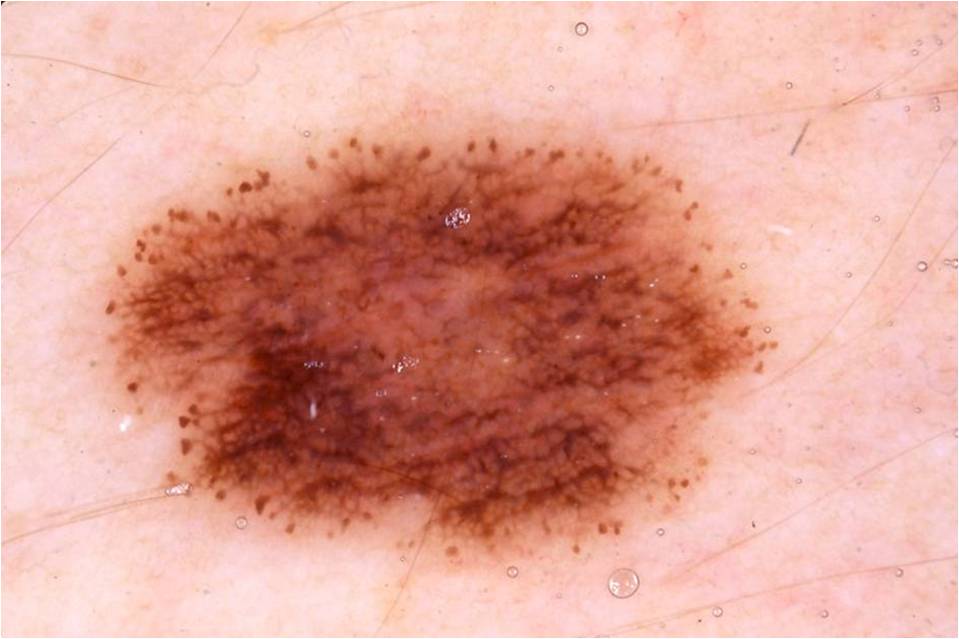<lesion>
<image>
  <modality>dermoscopy</modality>
</image>
<lesion_location>
  <bbox_xyxy>96, 123, 786, 578</bbox_xyxy>
</lesion_location>
<lesion_extent>large</lesion_extent>
<diagnosis>
  <malignancy>benign</malignancy>
  <provenance>clinical</provenance>
</diagnosis>
</lesion>